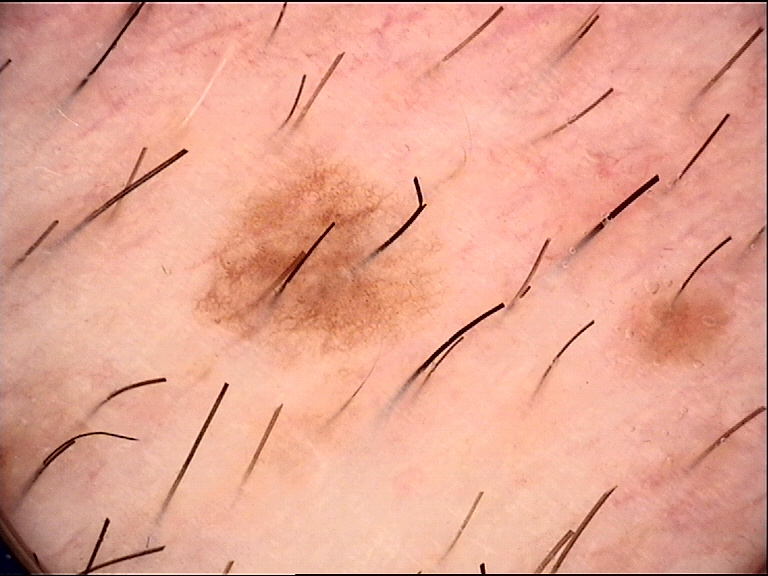Classified as a dysplastic junctional nevus.